A dermoscopy image of a single skin lesion · the subject is a female aged around 60: 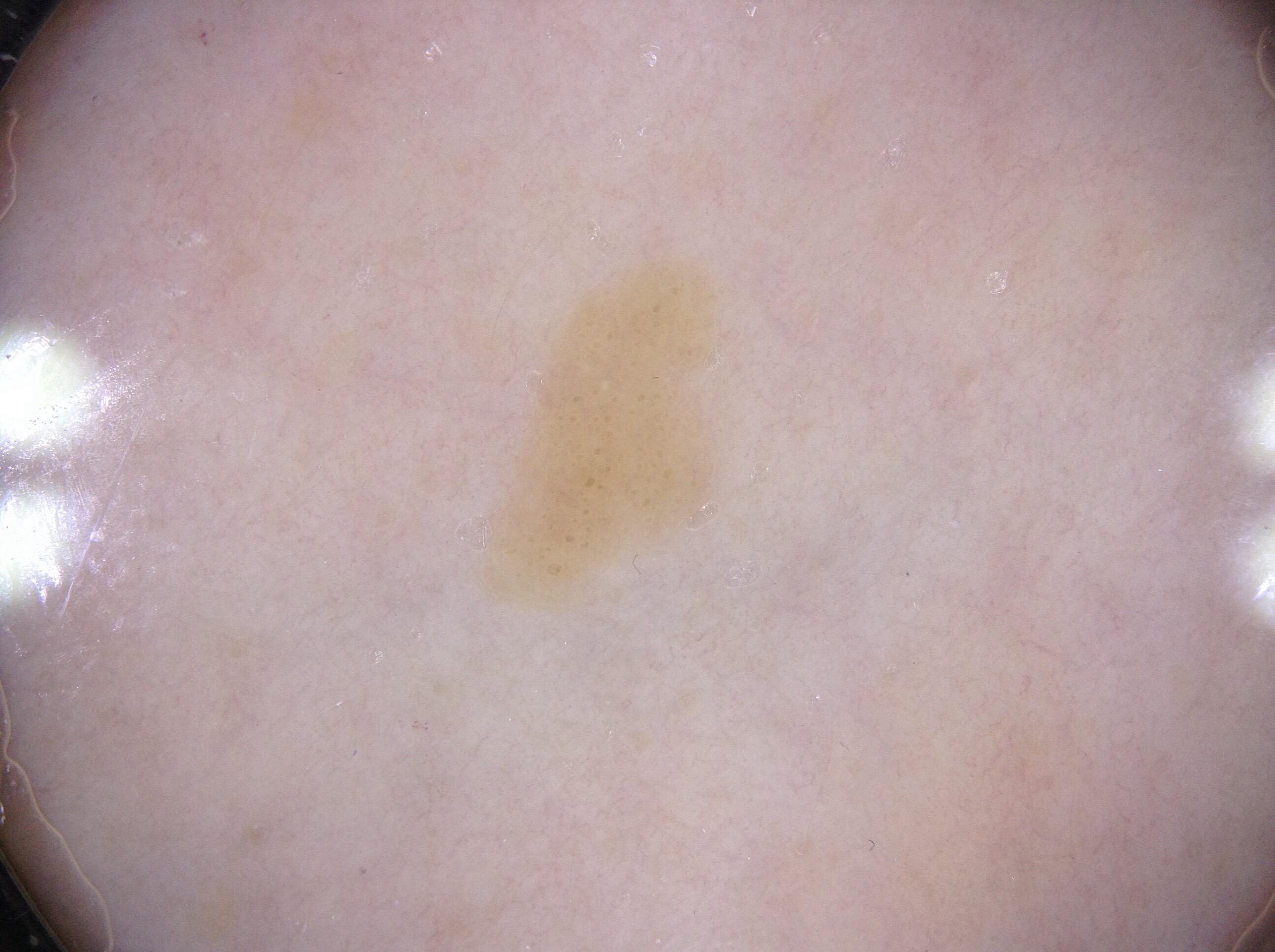| feature | finding |
|---|---|
| bounding box | x1=473, y1=242, x2=729, y2=615 |
| dermoscopic findings | milia-like cysts; absent: streaks, negative network, and pigment network |
| diagnostic label | a seborrheic keratosis, a benign skin lesion |